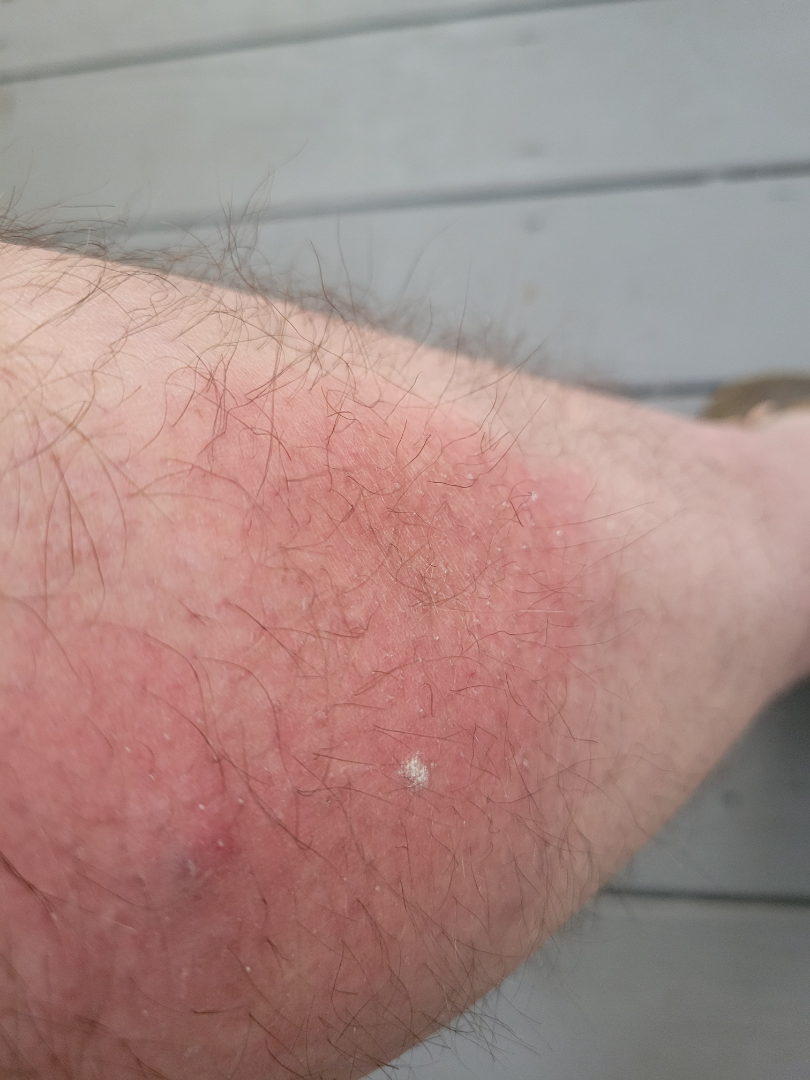differential diagnosis = the leading impression is Cellulitis; an alternative is Eczema; also raised was Necrobiosis lipoidica.